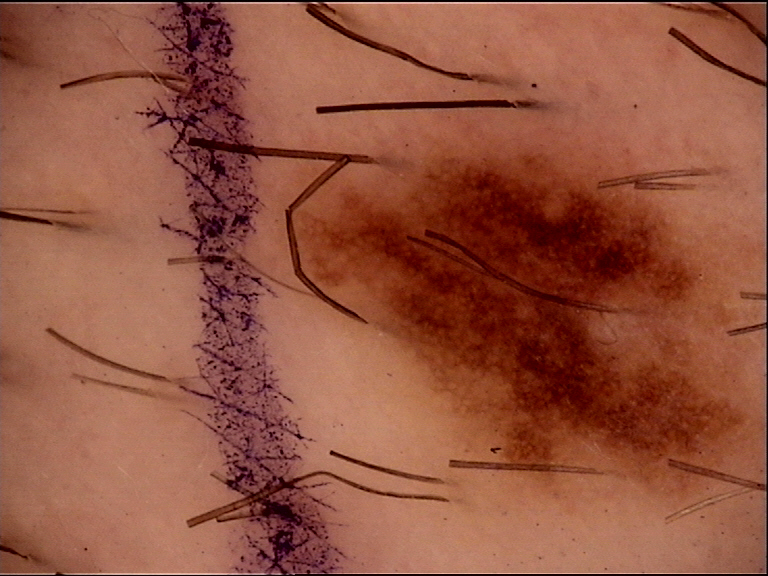| key | value |
|---|---|
| label | dysplastic junctional nevus (expert consensus) |